A dermoscopic photograph of a skin lesion:
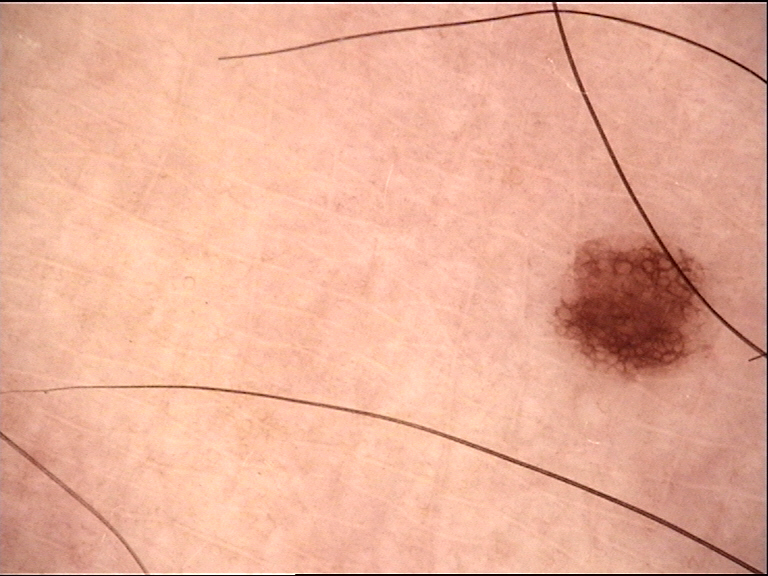Labeled as a dysplastic junctional nevus.